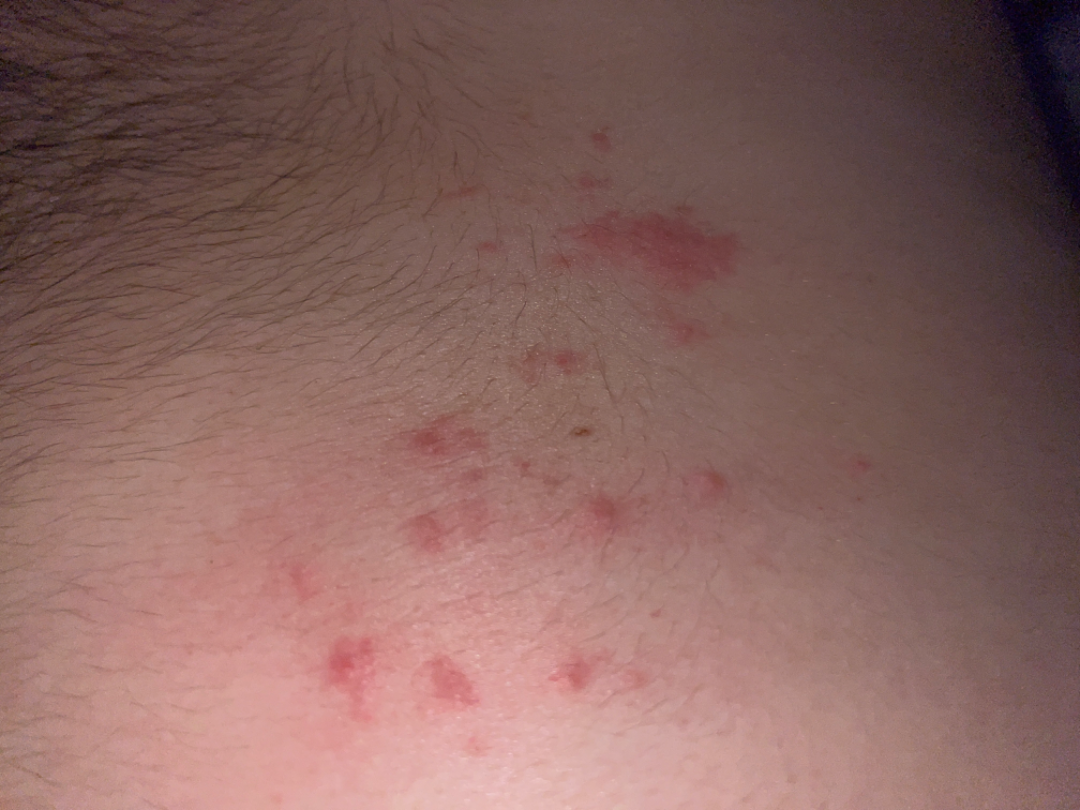location: head or neck, leg, arm, front of the torso and top or side of the foot | patient: male, age 18–29 | framing: close-up | differential: Folliculitis, Herpes Zoster and Allergic Contact Dermatitis were each considered, in no particular order.